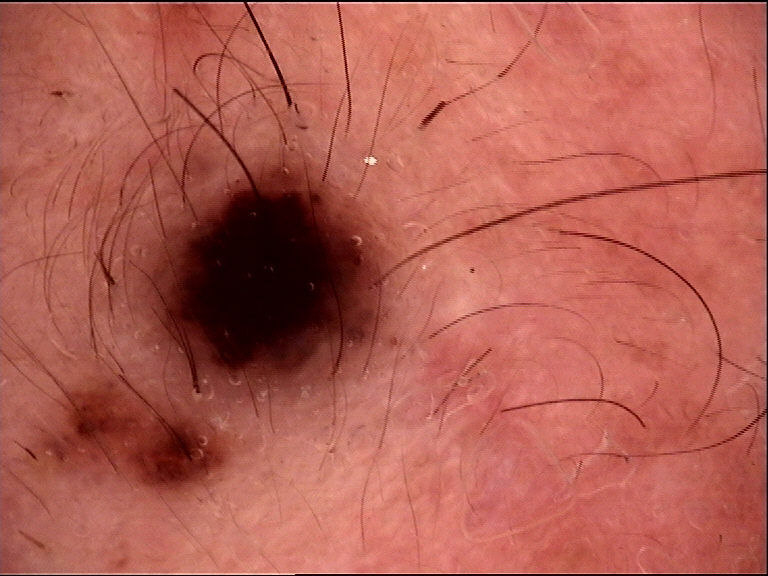diagnosis = compound nevus (expert consensus).